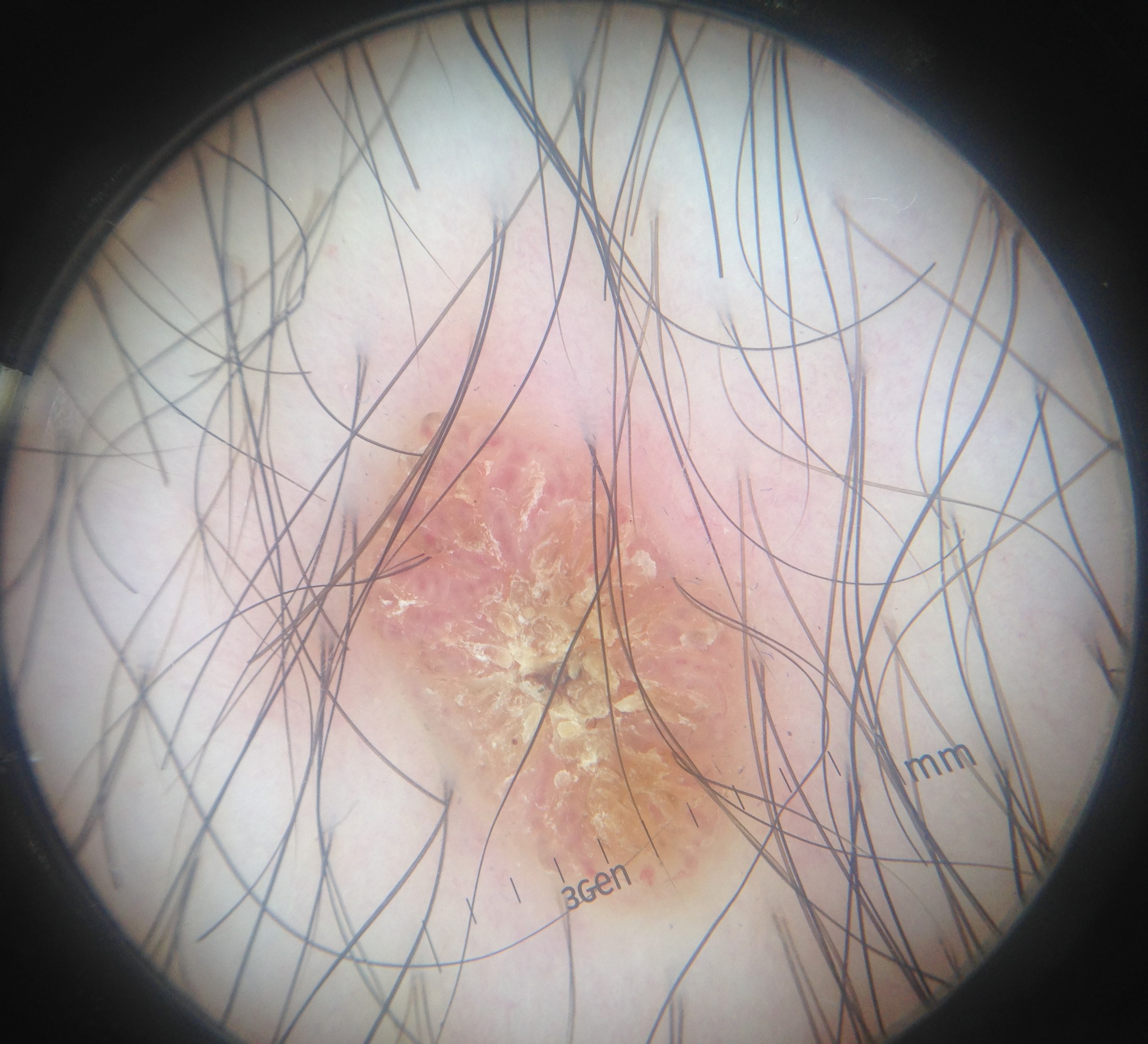Q: What is this lesion?
A: seborrheic keratosis (expert consensus)